An image taken at an angle — 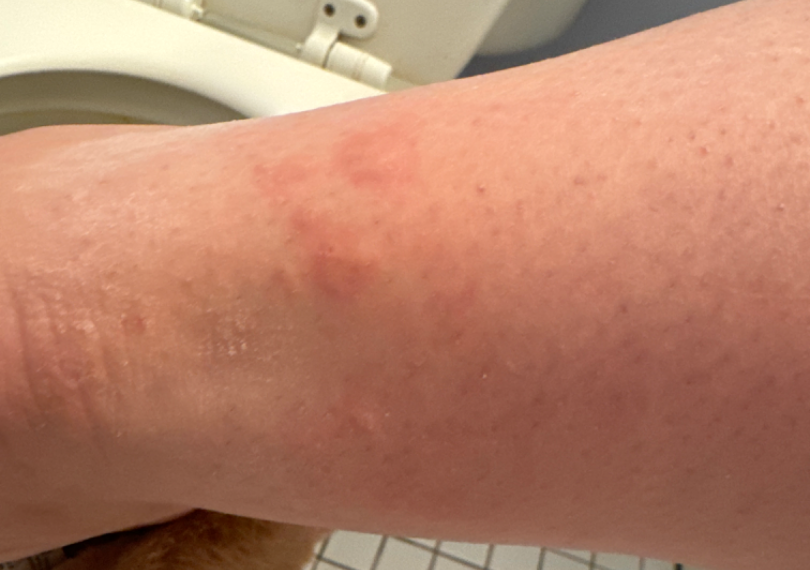| field | value |
|---|---|
| skin tone | Fitzpatrick II; lay reviewers estimated Monk Skin Tone 3 (US pool) or 2 (India pool) |
| present for | less than one week |
| patient's own categorization | a rash |
| differential | the leading impression is Insect Bite; also consider Urticaria; possibly Animal bite - wound |